A dermatoscopic image of a skin lesion.
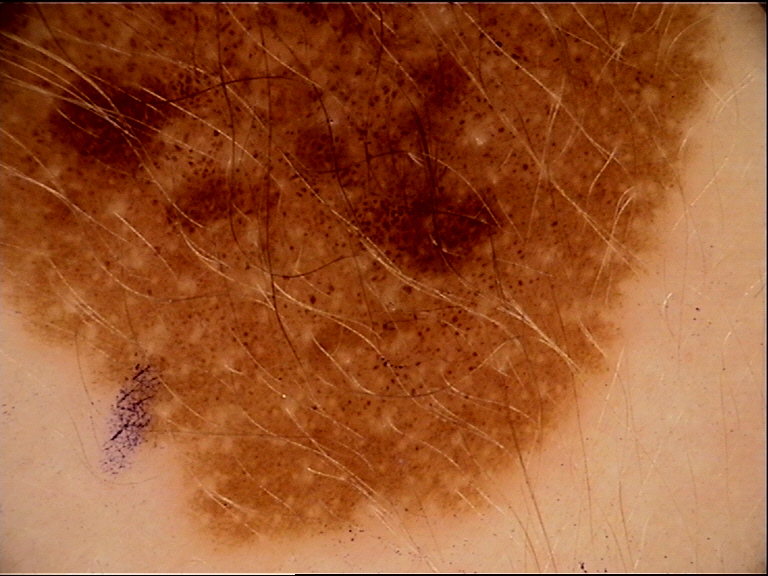The architecture is that of a banal lesion. Diagnosed as a congenital junctional nevus.